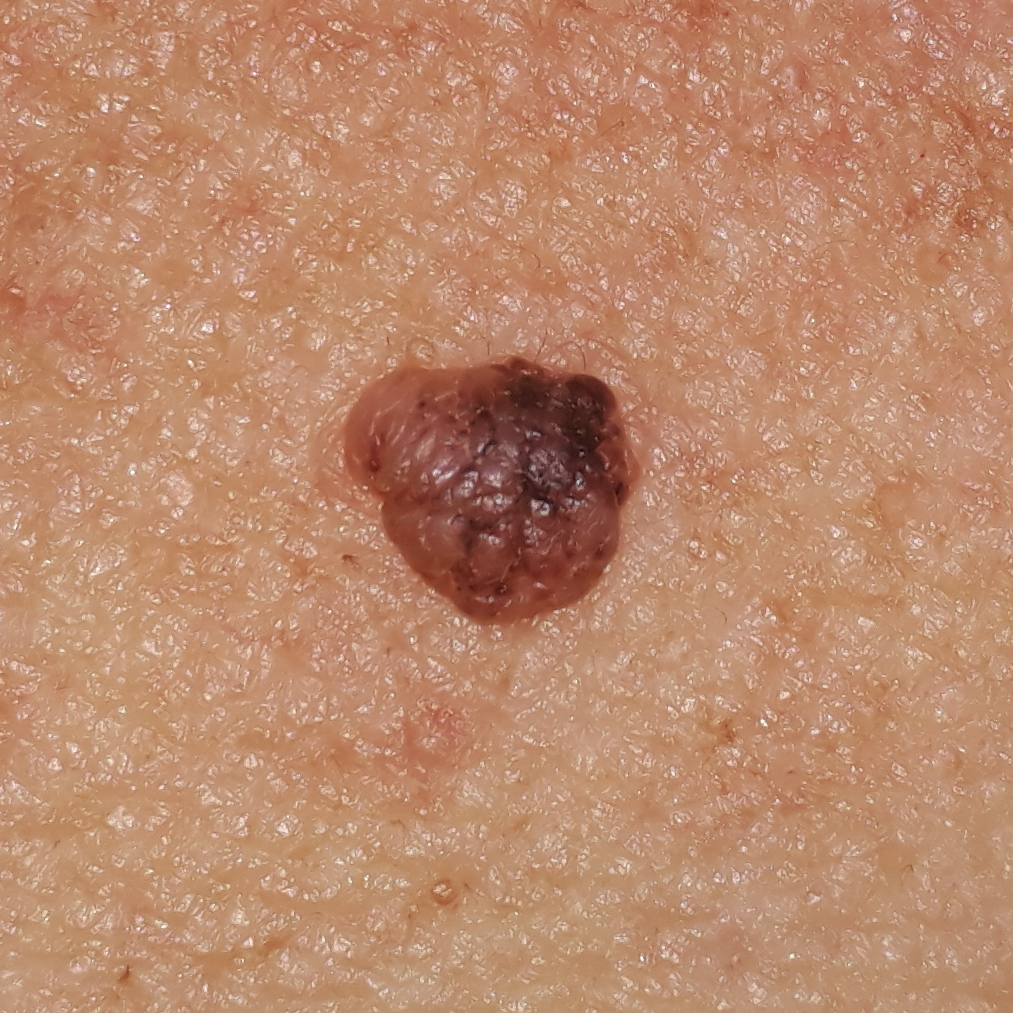A subject age 56. The lesion involves the chest. Diagnosed by dermatologist consensus as a nevus.